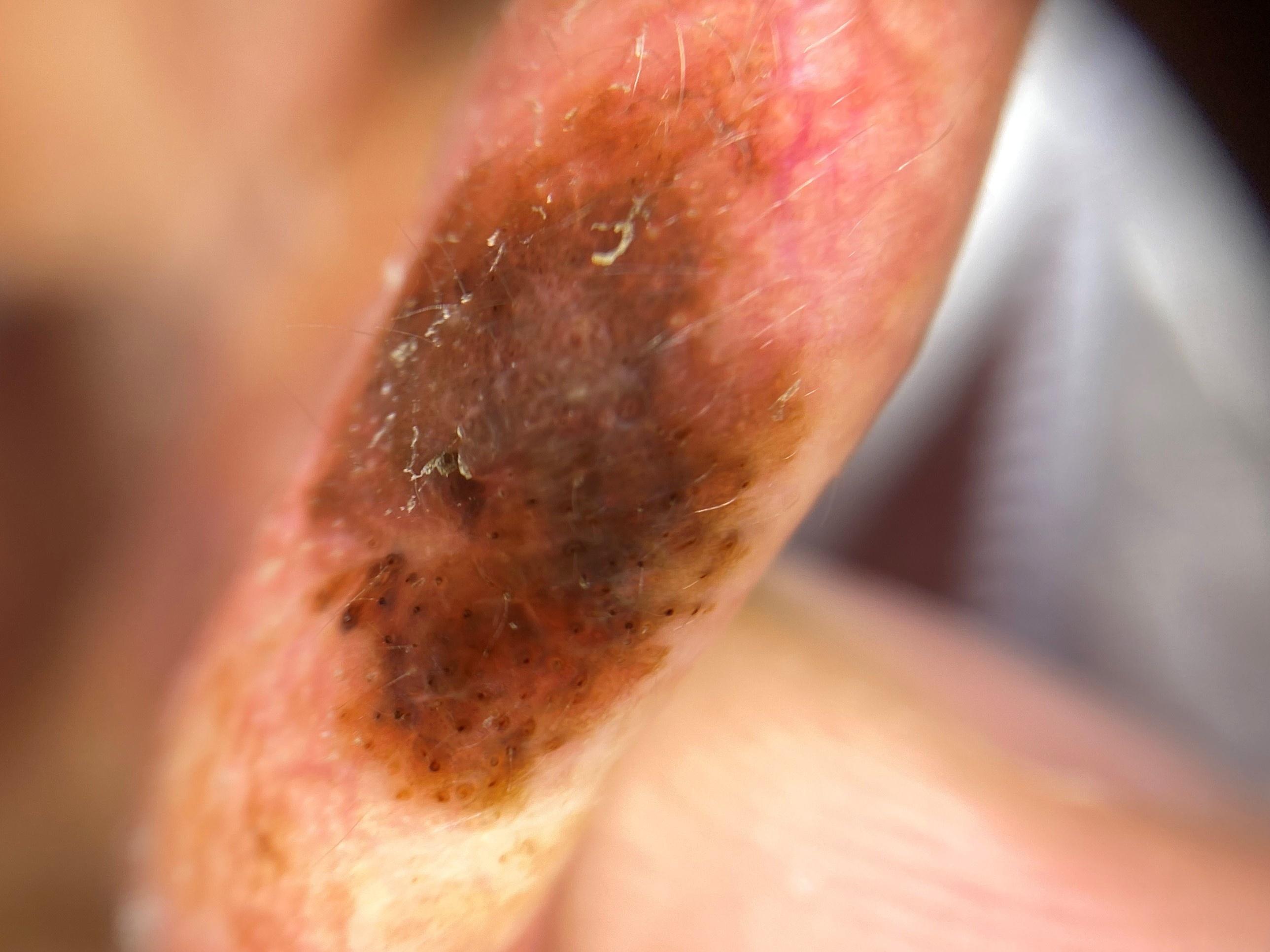A skin lesion imaged with a dermatoscope. A male subject aged around 75. The chart documents a prior melanoma. The lesion is located on the head or neck. The biopsy diagnosis was a melanoma.